A dermoscopy image of a single skin lesion:
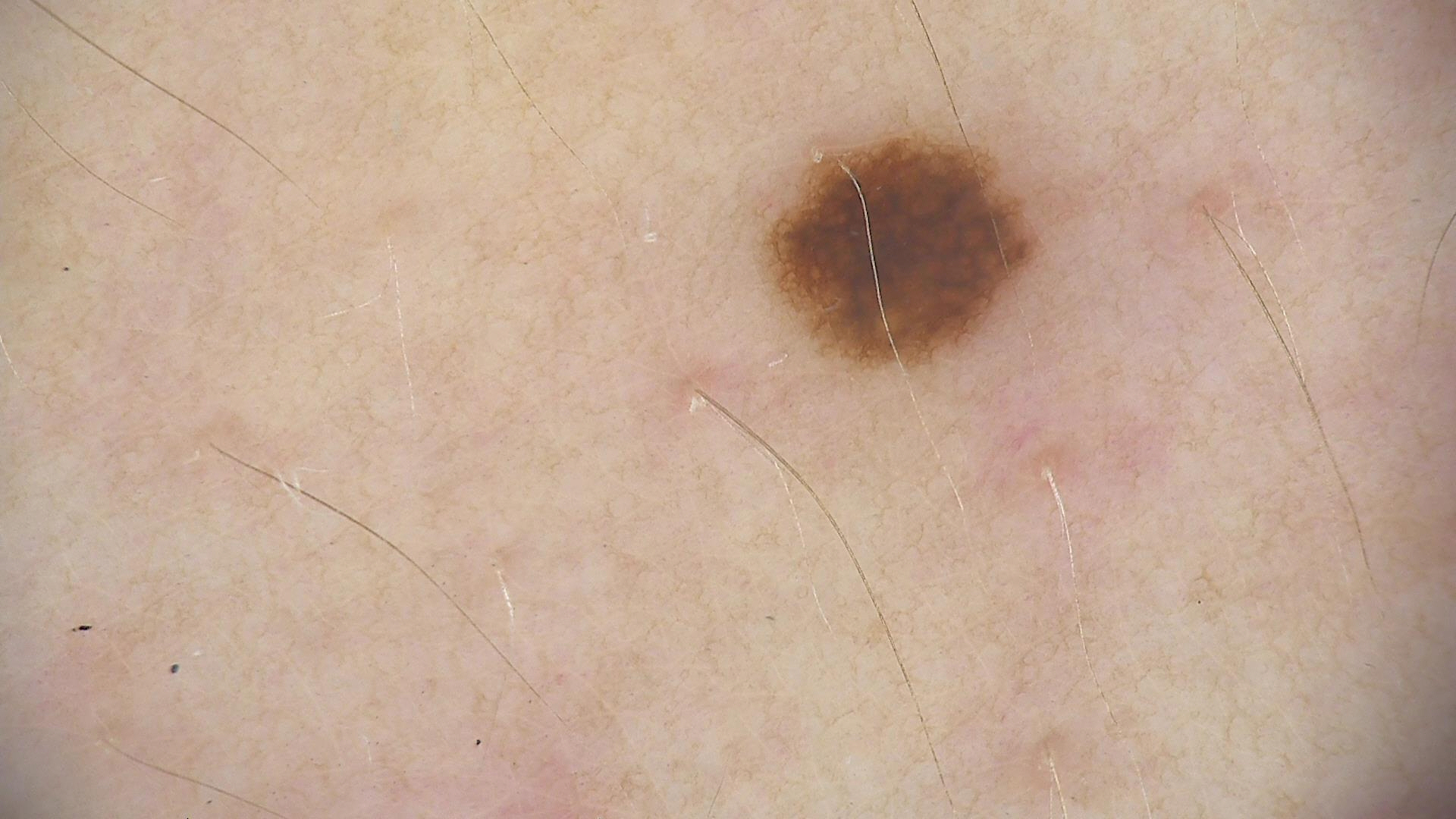<case>
  <diagnosis>
    <name>dysplastic junctional nevus</name>
    <code>jd</code>
    <malignancy>benign</malignancy>
    <super_class>melanocytic</super_class>
    <confirmation>expert consensus</confirmation>
  </diagnosis>
</case>